A female patient aged 78. The patient says their skin tans without first burning. A dermoscopic image of a skin lesion:
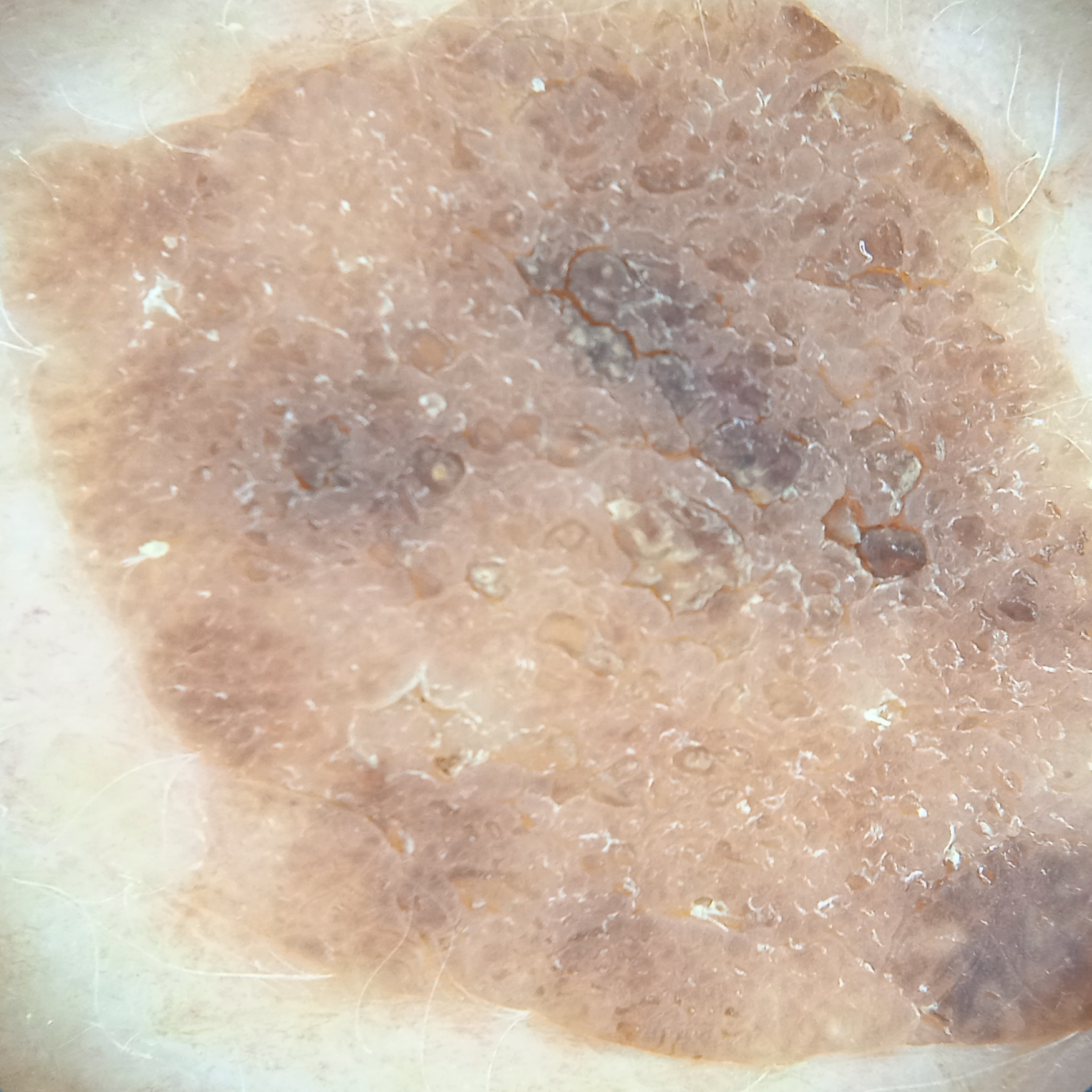{"lesion_size": {"diameter_mm": 15.7}, "diagnosis": {"name": "seborrheic keratosis", "malignancy": "benign"}}